No associated systemic symptoms reported; the photo was captured at a distance; the patient considered this a rash; the subject is 30–39, female; symptoms reported: itching; the patient notes the condition has been present for one to four weeks; texture is reported as rough or flaky and raised or bumpy:
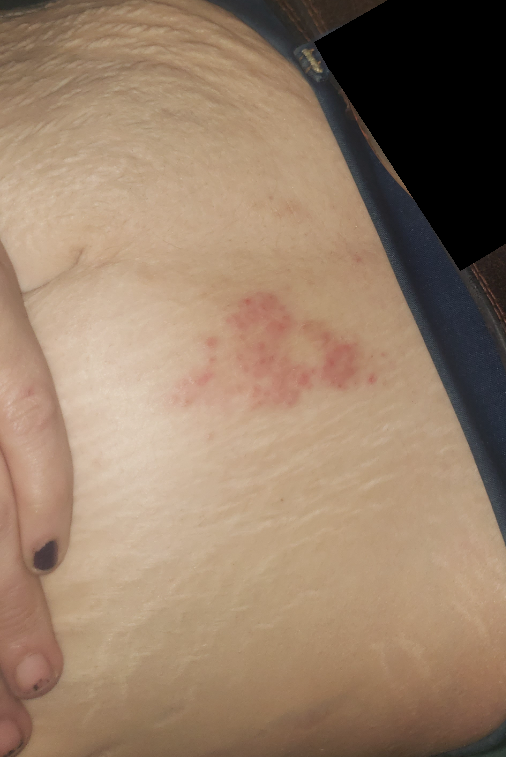{"differential": {"leading": ["Herpes Zoster"], "considered": ["Tinea", "Impetigo"]}}